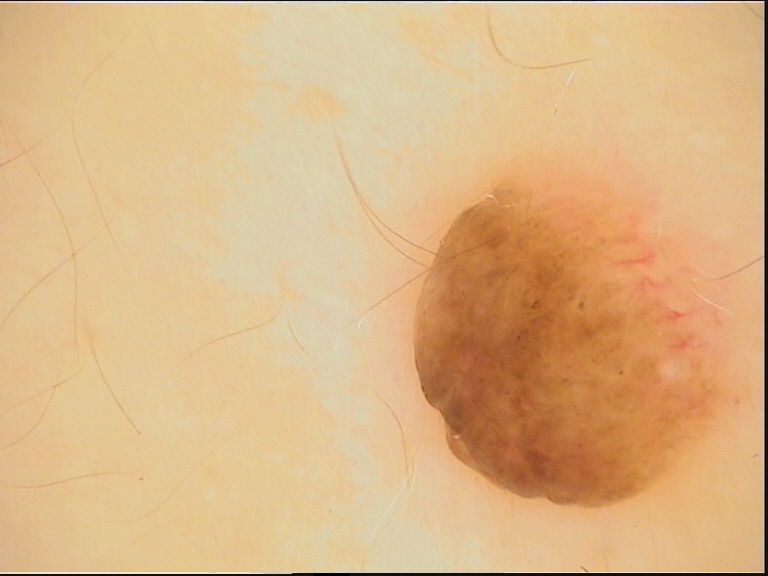image: dermatoscopy
lesion_type:
  main_class: banal
  pattern: dermal
diagnosis:
  name: dermal nevus
  code: db
  malignancy: benign
  super_class: melanocytic
  confirmation: expert consensus